A male subject approximately 75 years of age. The patient is Fitzpatrick III. A clinical photograph of a skin lesion — 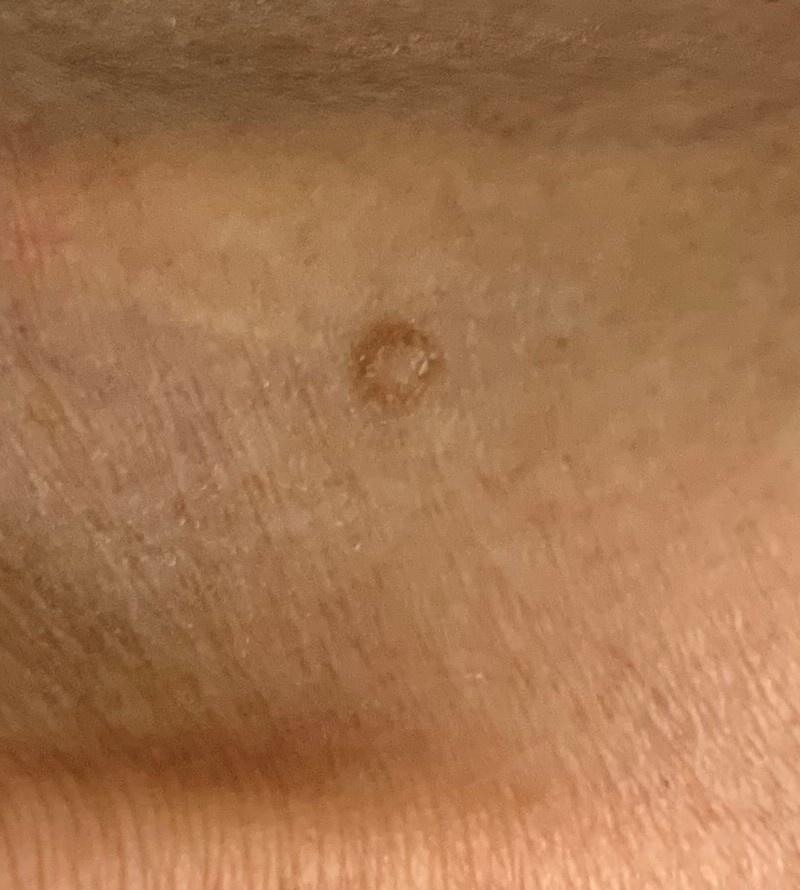The clinical impression was a lesion of fibro-histiocytic origin — a dermatofibroma.